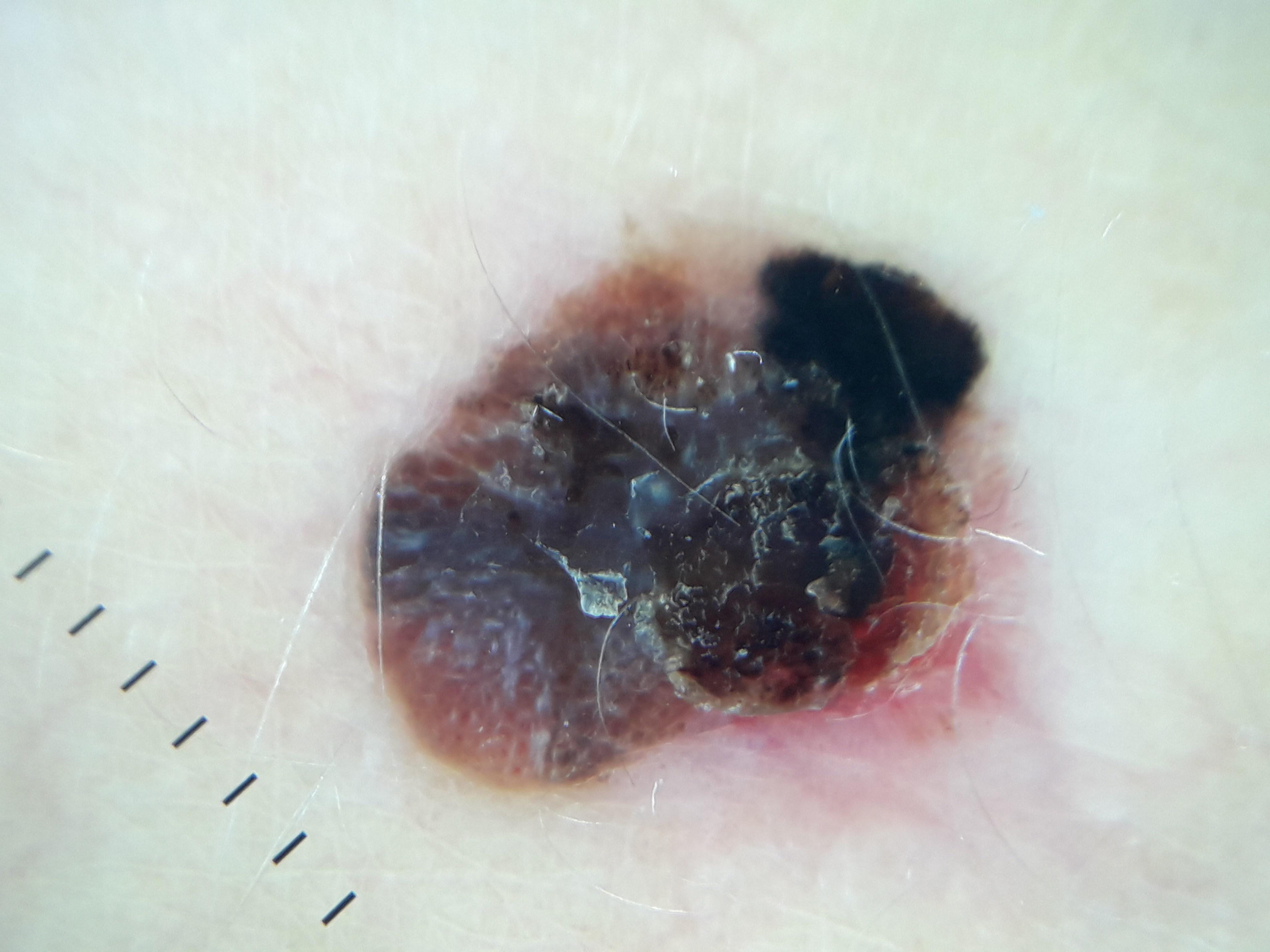A female subject approximately 35 years of age.
The chart notes a previous melanoma but no first-degree relative with melanoma.
Dermoscopy of a skin lesion.
The biopsy diagnosis was a skin cancer — a melanoma.